The lesion involves the leg · this is a close-up image · male patient, age 30–39 — 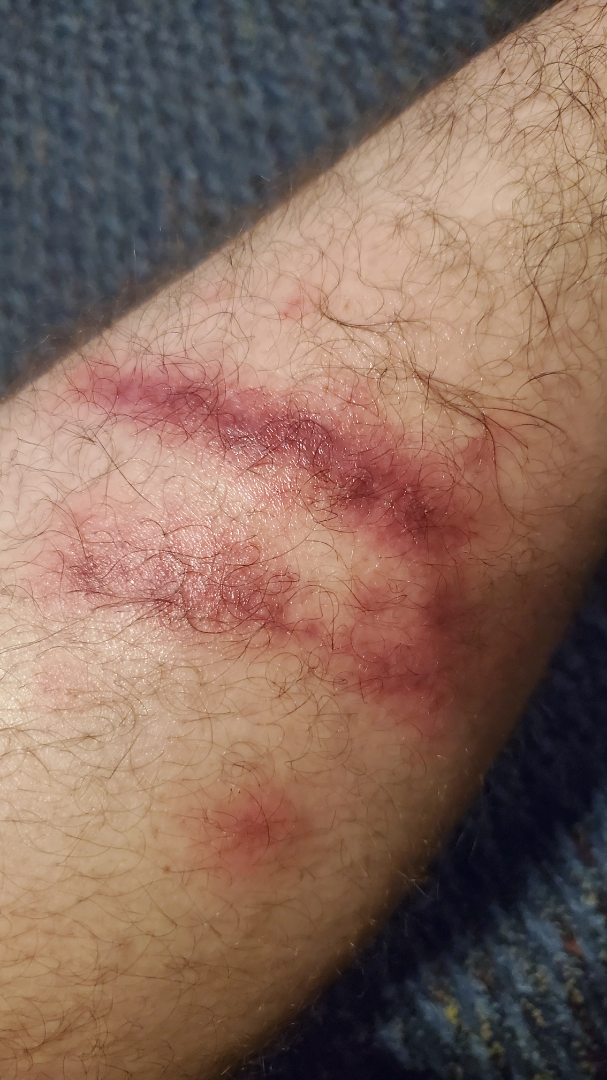On teledermatology review: the differential is split between Abrasion, scrape, or scab and Flagellate erythema; a more distant consideration is Allergic Contact Dermatitis; less probable is Skin infection; less likely is Dermatomyositis; lower on the differential is Animal bite - wound.